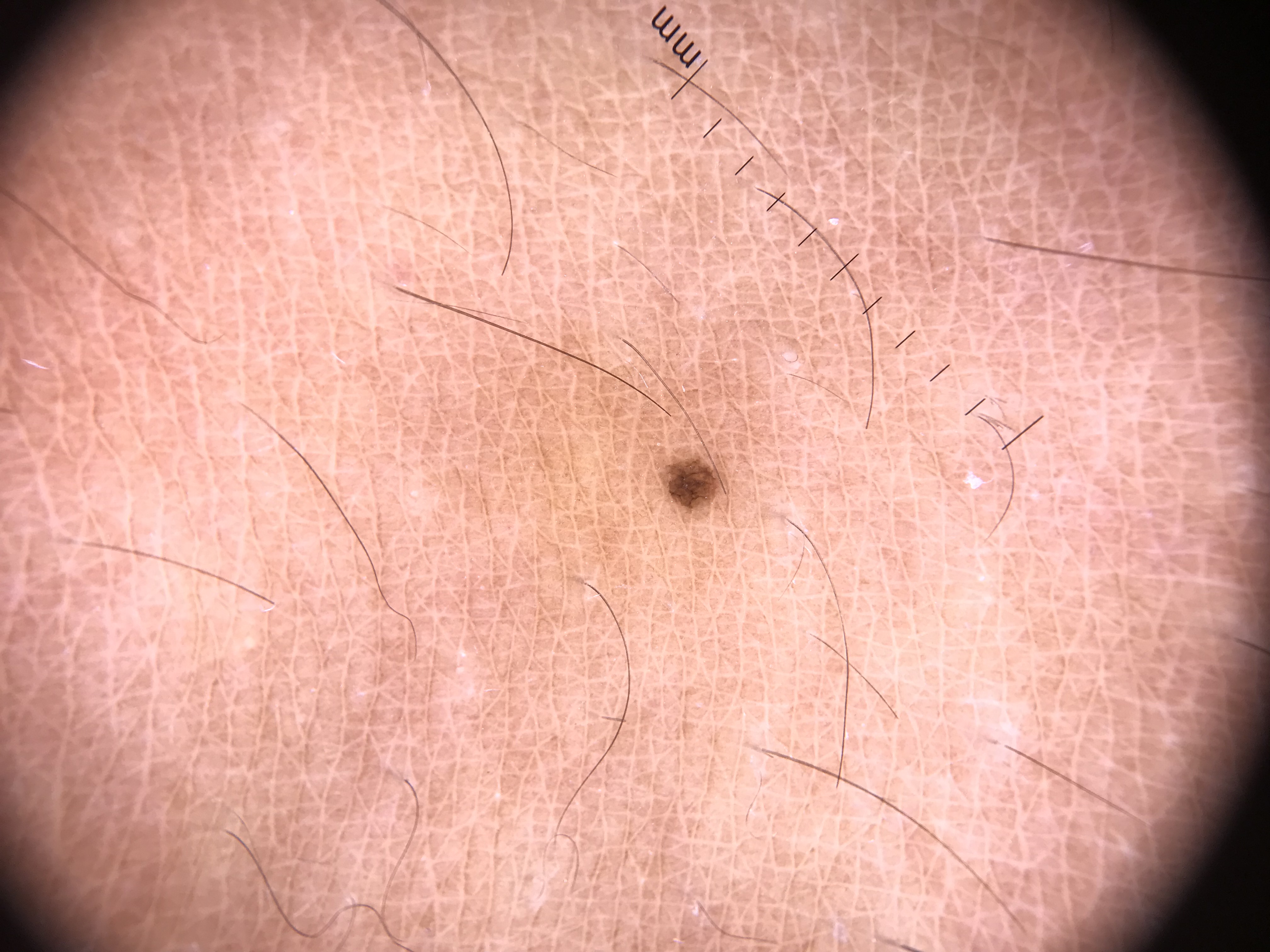A dermoscopic image of a skin lesion.
The architecture is that of a banal lesion.
Consistent with a junctional nevus.